A female patient in their 70s.
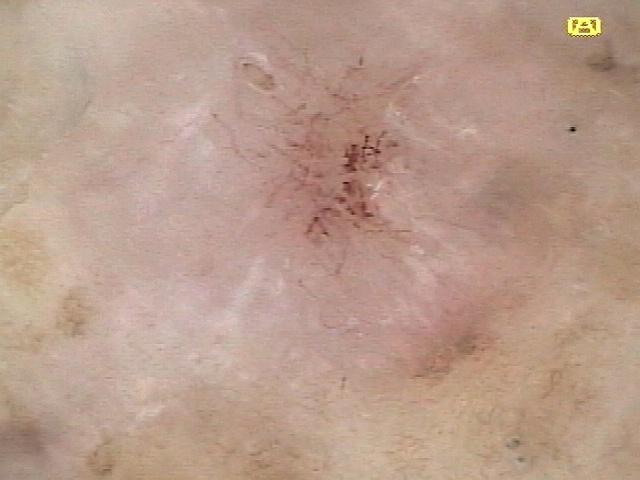Summary:
The lesion is located on a lower extremity.
Pathology:
On biopsy, the diagnosis was a basal cell carcinoma.